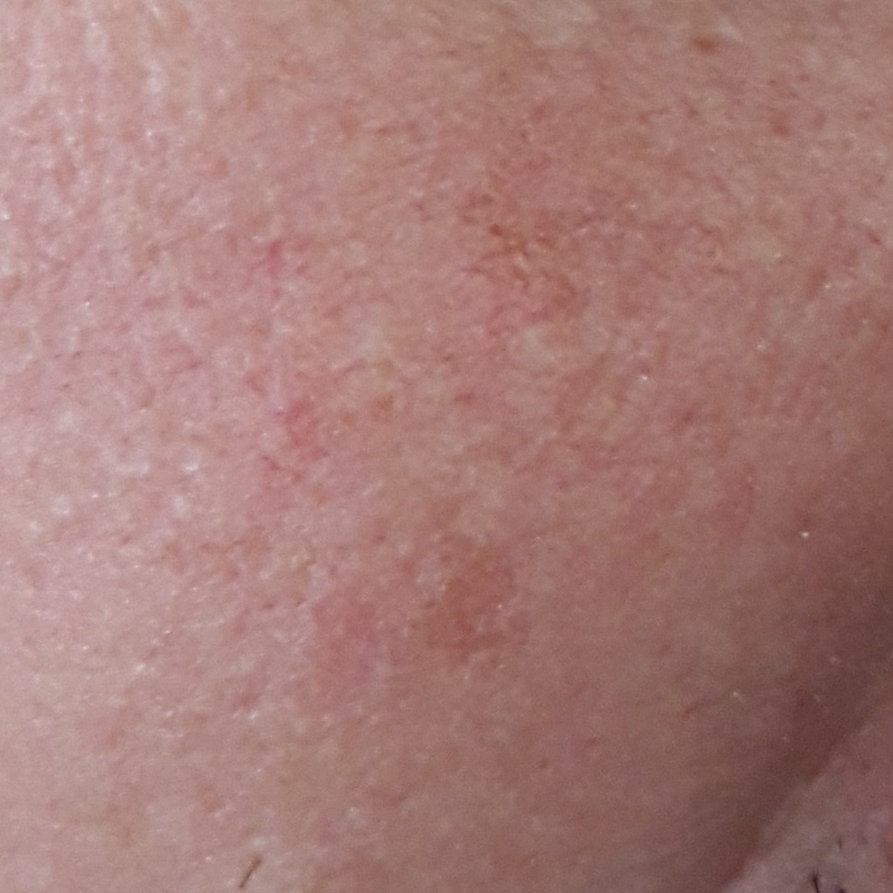Findings:
- image type · smartphone clinical photo
- patient · in their late 40s
- symptoms · pain, growth
- impression · actinic keratosis (clinical consensus)